A dermatoscopic image of a skin lesion. By self-report, a family history of skin cancer, a personal history of cancer, and no immunosuppression. Referred with a clinical suspicion of basal cell carcinoma — 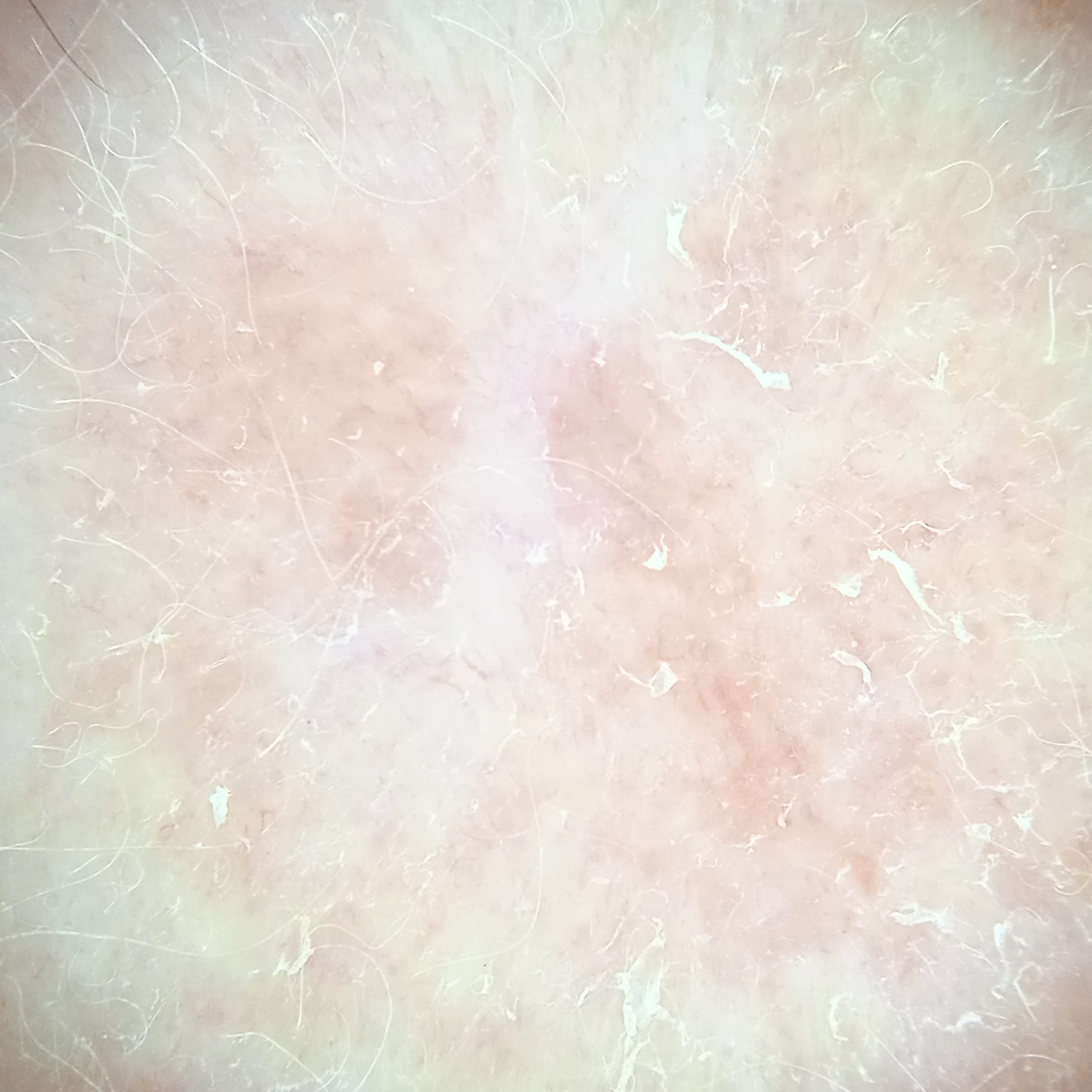Findings:
– anatomic site: the face
– diagnostic label: basal cell carcinoma (biopsy-proven)